The patient notes the lesion is raised or bumpy · female patient, age 40–49 · no associated systemic symptoms reported · located on the leg · the condition has been present for less than one week · the patient notes bothersome appearance, pain, enlargement, burning and itching · the patient described the issue as a rash · an image taken at an angle: 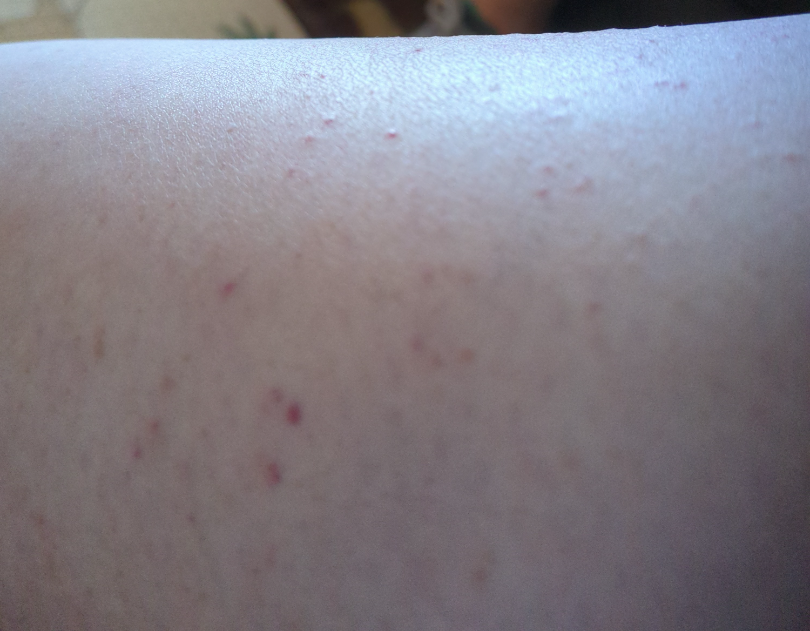On remote dermatologist review, Leukocytoclastic Vasculitis (favored); Pigmented purpuric eruption (possible).